The affected area is the leg and front of the torso; the contributor is a female aged 50–59; this image was taken at an angle:
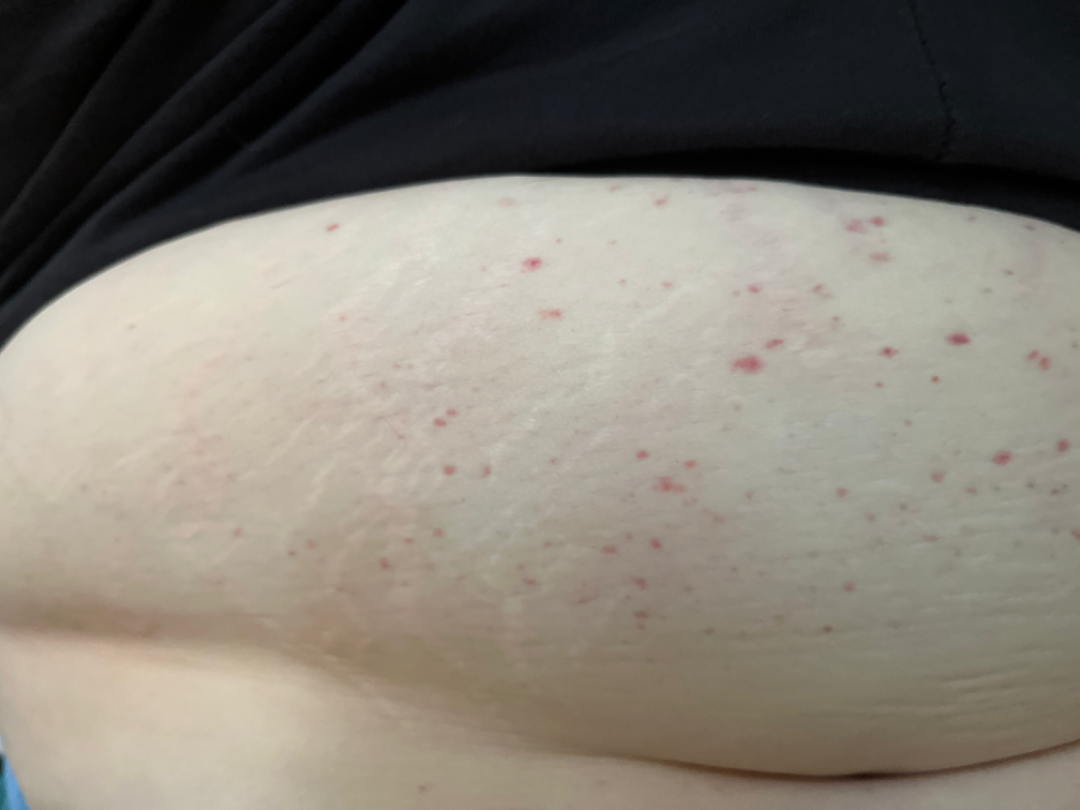  assessment: indeterminate from the photograph